The lesion involves the arm and leg, this is a close-up image:
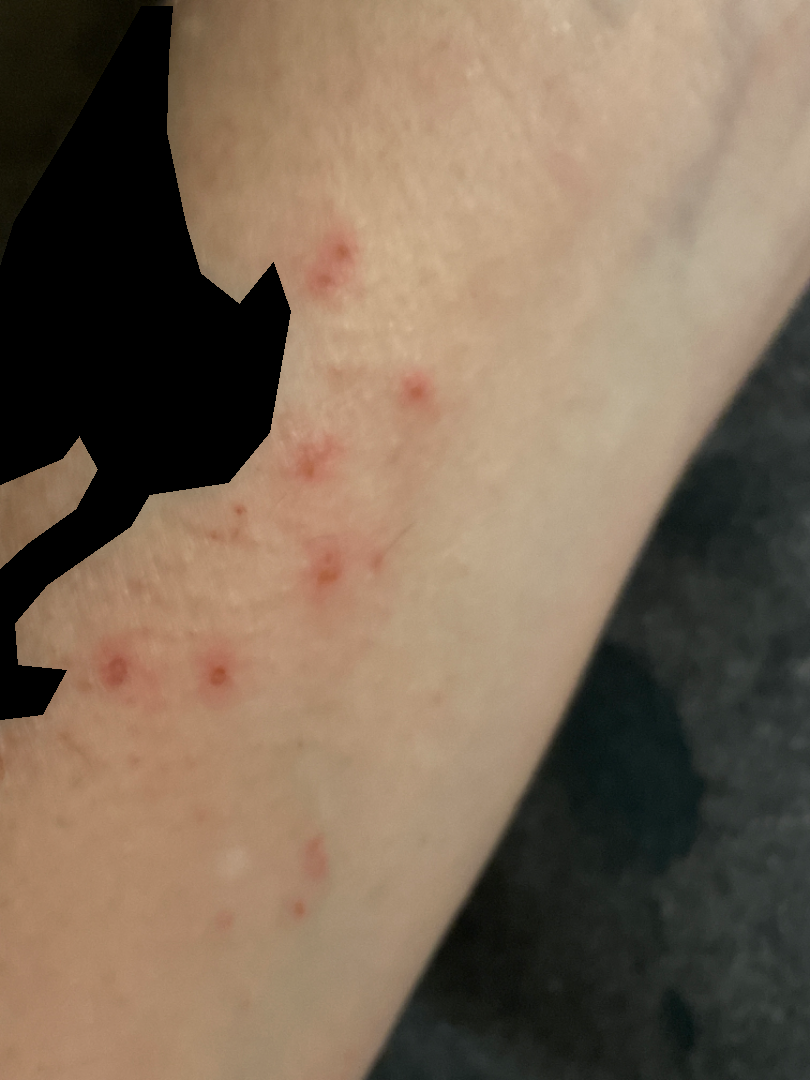Findings:
* assessment: unable to determine
* self-categorized as: a rash
* duration: one to four weeks
* systemic symptoms: none reported
* surface texture: rough or flaky